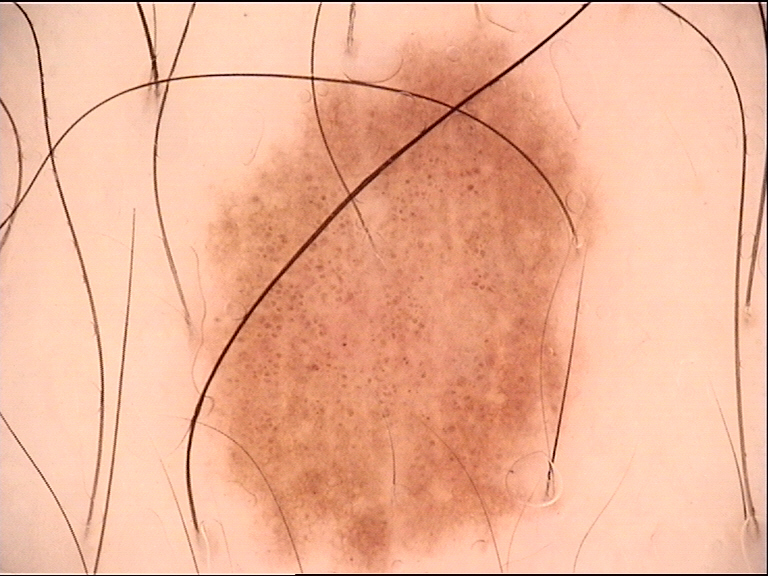Labeled as a benign lesion — a dysplastic junctional nevus.